The photo was captured at an angle:
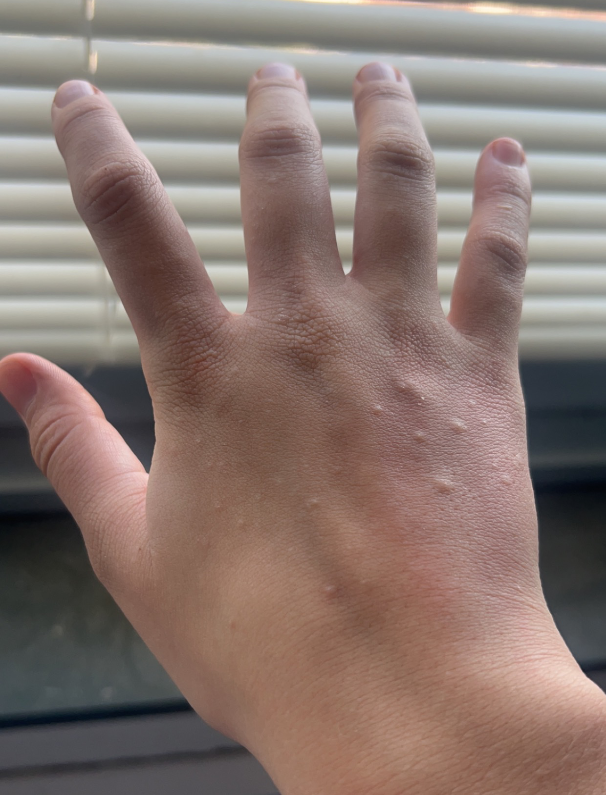The lesion is associated with itching and bothersome appearance. Fitzpatrick skin type III. On photographic review: the leading impression is Molluscum Contagiosum; also raised was Granuloma annulare; lower on the differential is Keratoderma.